A dermoscopy image of a single skin lesion.
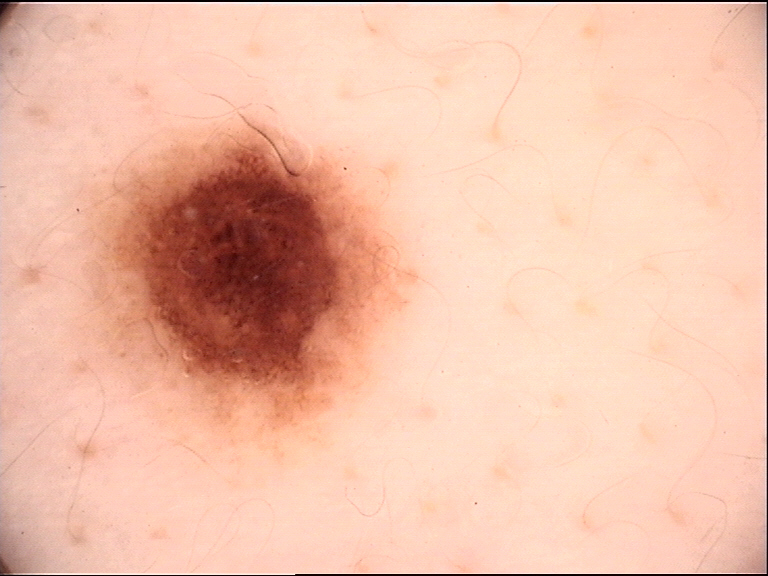Classified as a banal lesion — a junctional nevus.